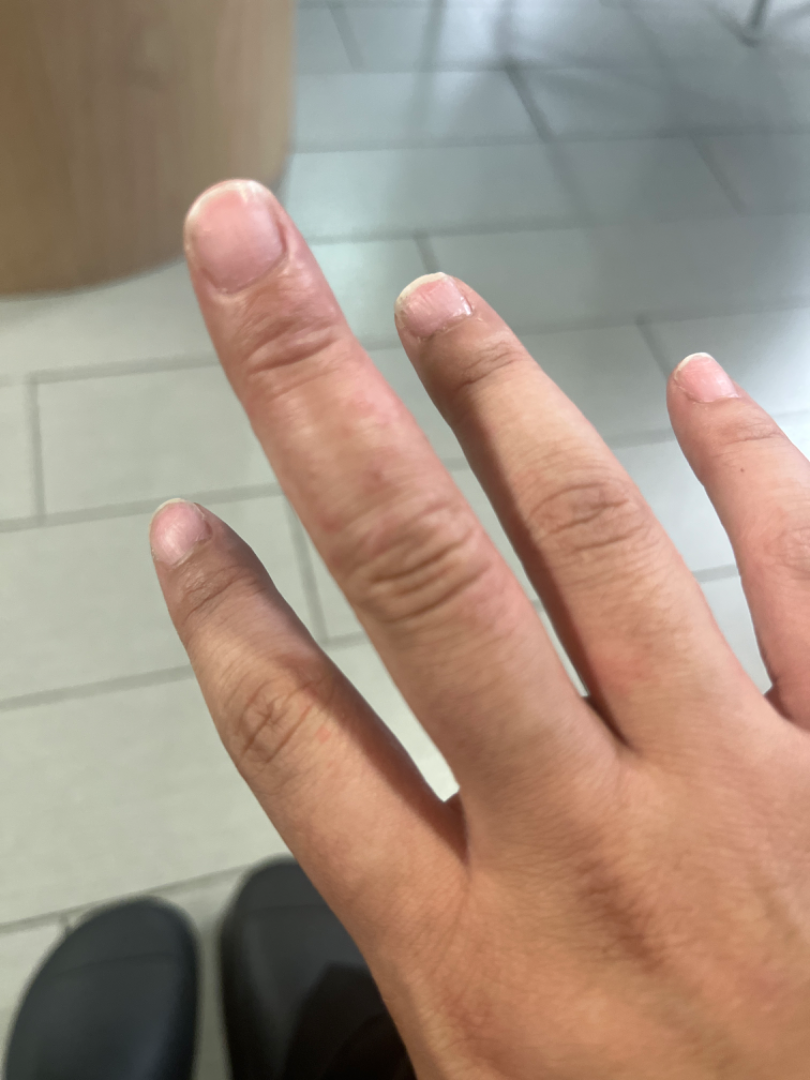Located on the palm and back of the hand.
This is a close-up image.
The contributor is 18–29, female.
On photographic review by a dermatologist, the leading consideration is Eczema; possibly Allergic Contact Dermatitis.